A dermoscopic image of a skin lesion: 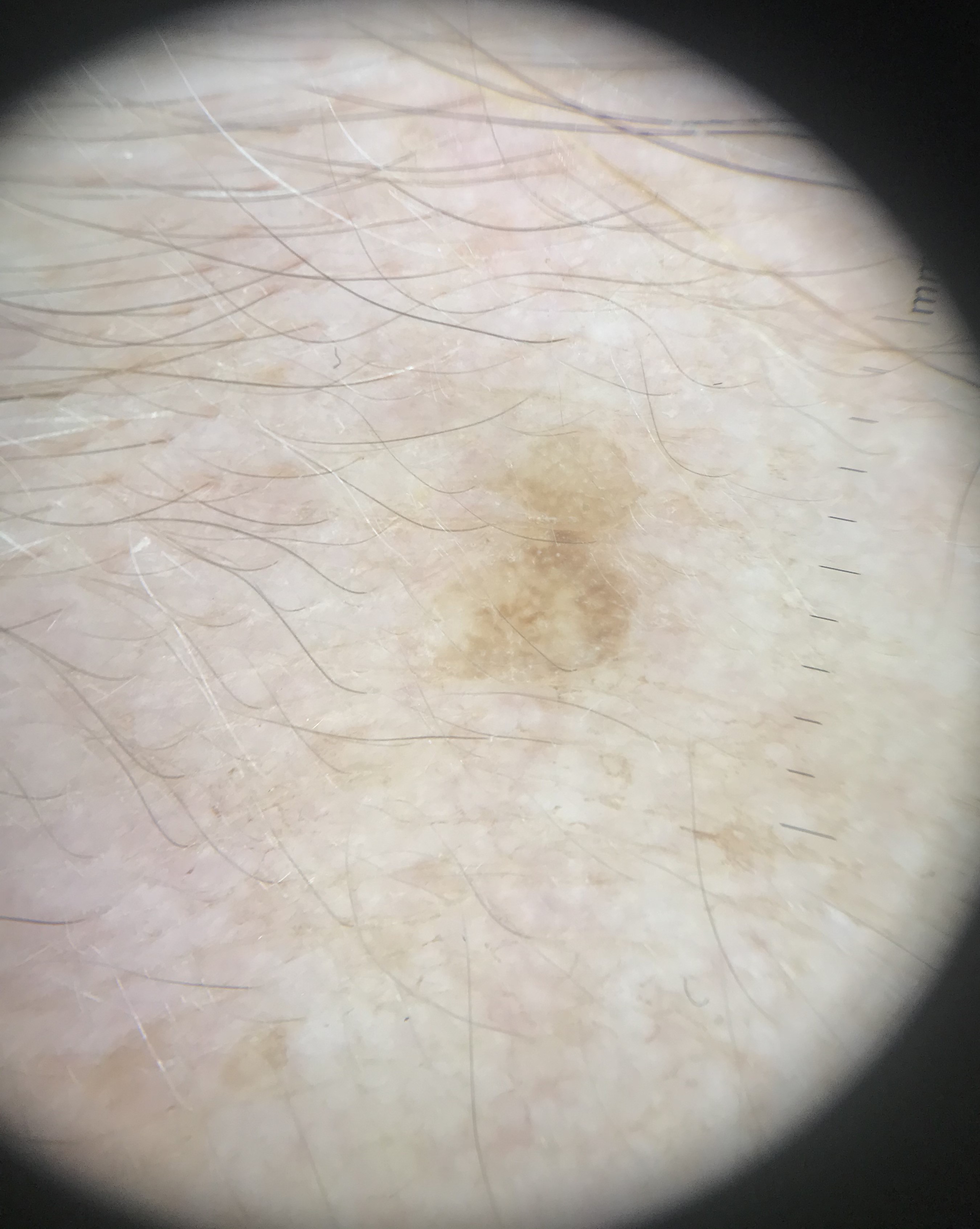Case:
* classification · keratinocytic
* assessment · seborrheic keratosis (expert consensus)